The patient is female. The photo was captured at an angle:
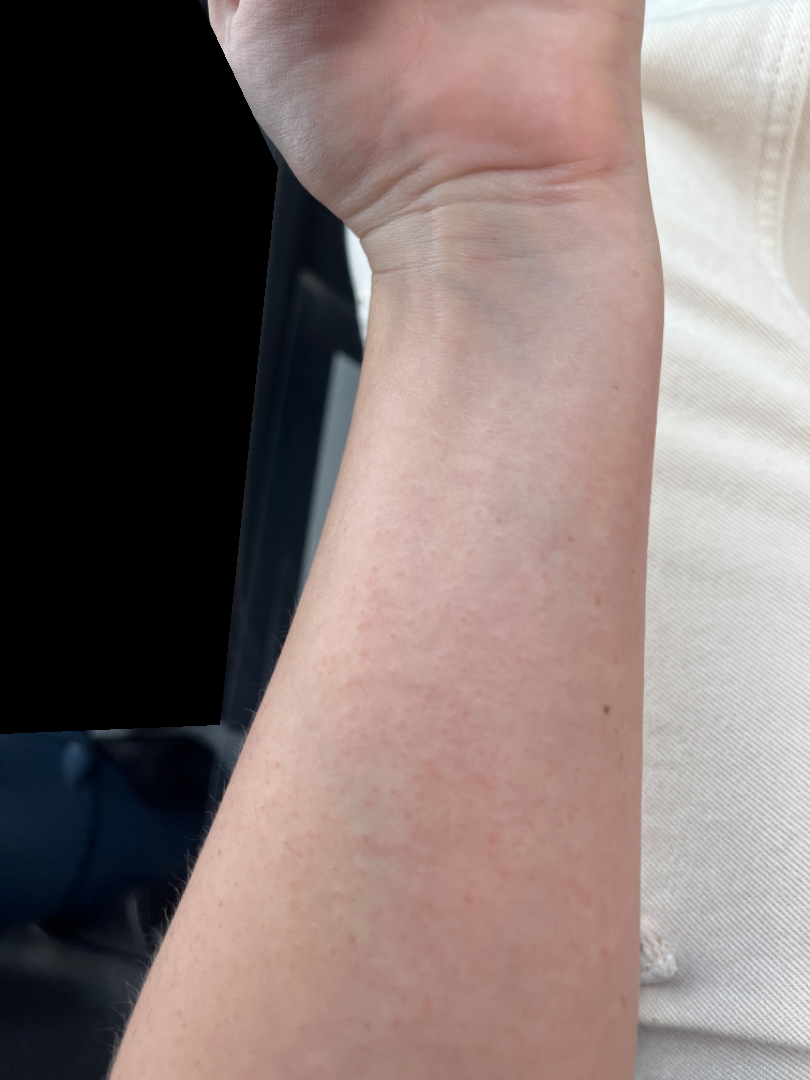| field | value |
|---|---|
| assessment | ungradable on photographic review |